The affected area is the front of the torso, this is a close-up image, the subject is male — 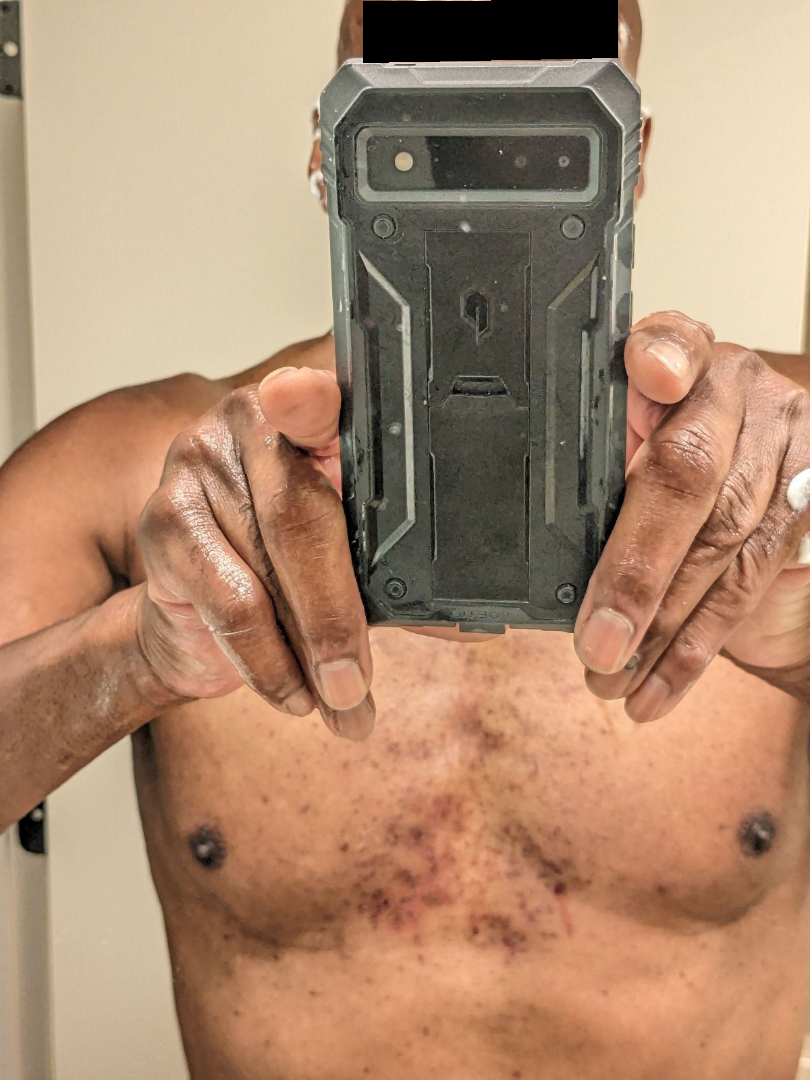The skin condition could not be confidently assessed from this image.